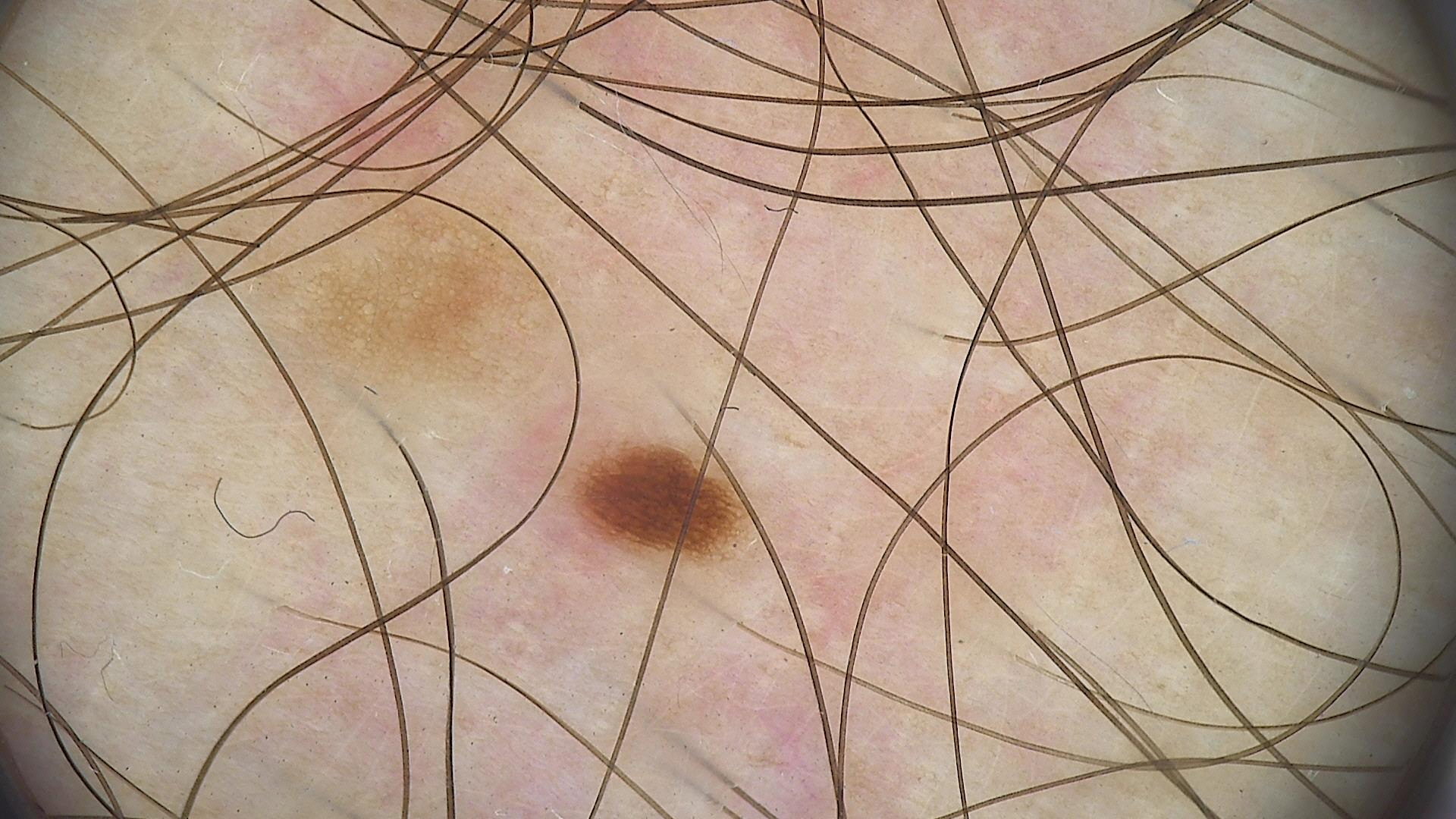A dermoscopic close-up of a skin lesion. This is a banal lesion. The diagnosis was a junctional nevus.